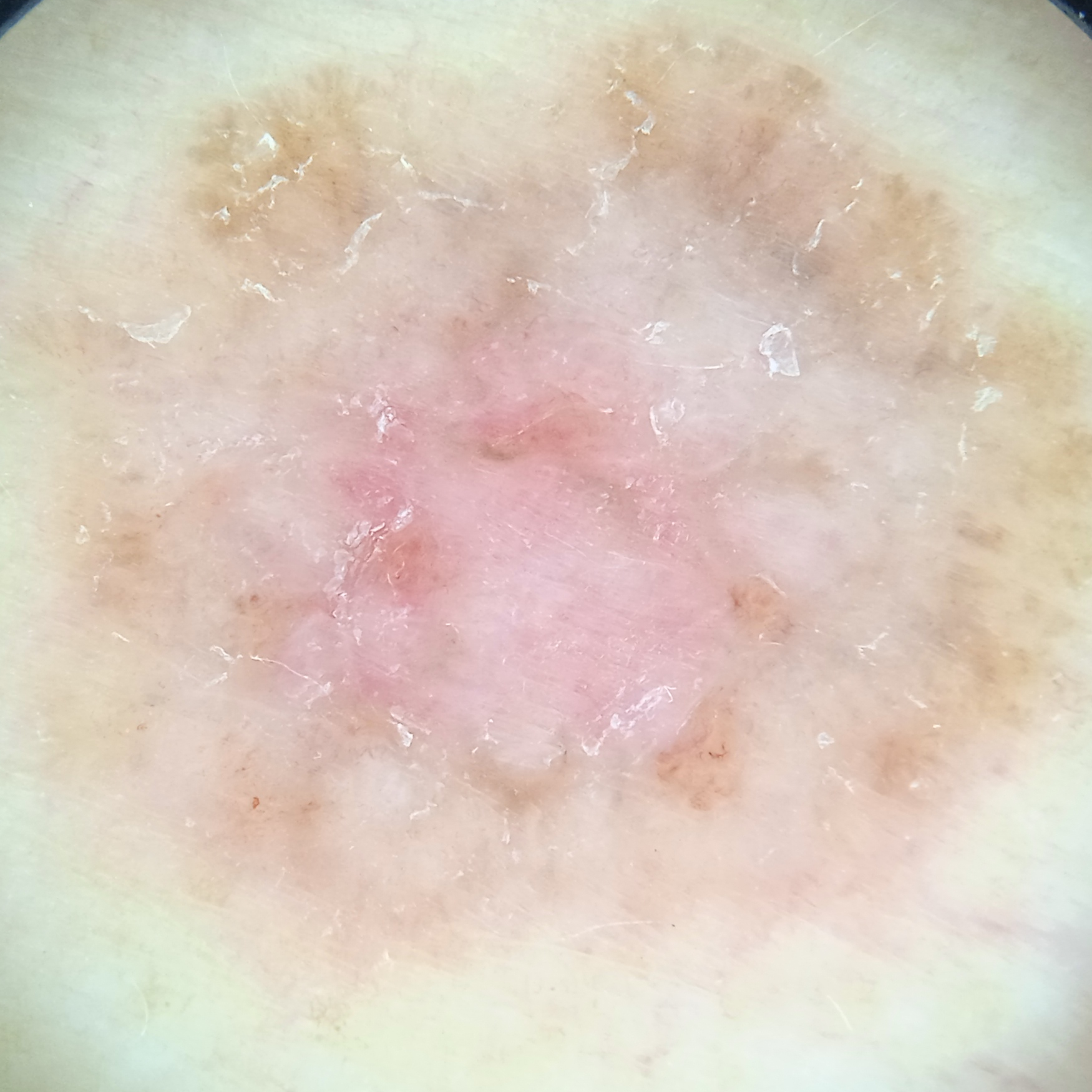{"image": "dermoscopy", "referral": "clinical suspicion of basal cell carcinoma", "patient": {"age": 60, "sex": "female"}, "lesion_location": "the torso", "lesion_size": {"diameter_mm": 13.2}, "diagnosis": {"name": "basal cell carcinoma", "malignancy": "malignant"}}